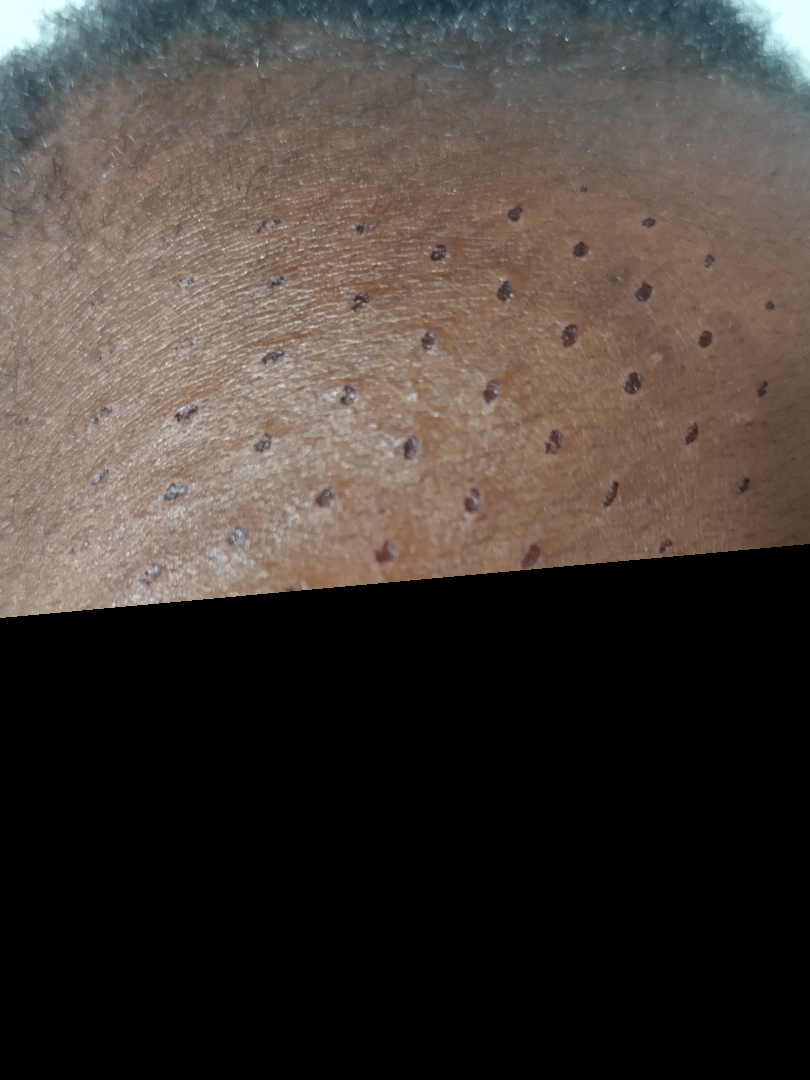Case summary:
• assessment — could not be assessed
• image framing — close-up
• anatomic site — head or neck
• patient's own categorization — a rash
• subject — male